The patient described the issue as a rash; the contributor is a female aged 18–29; present for less than one week; the lesion involves the leg; symptoms reported: darkening, enlargement, itching and bothersome appearance; Fitzpatrick skin type I; this is a close-up image.
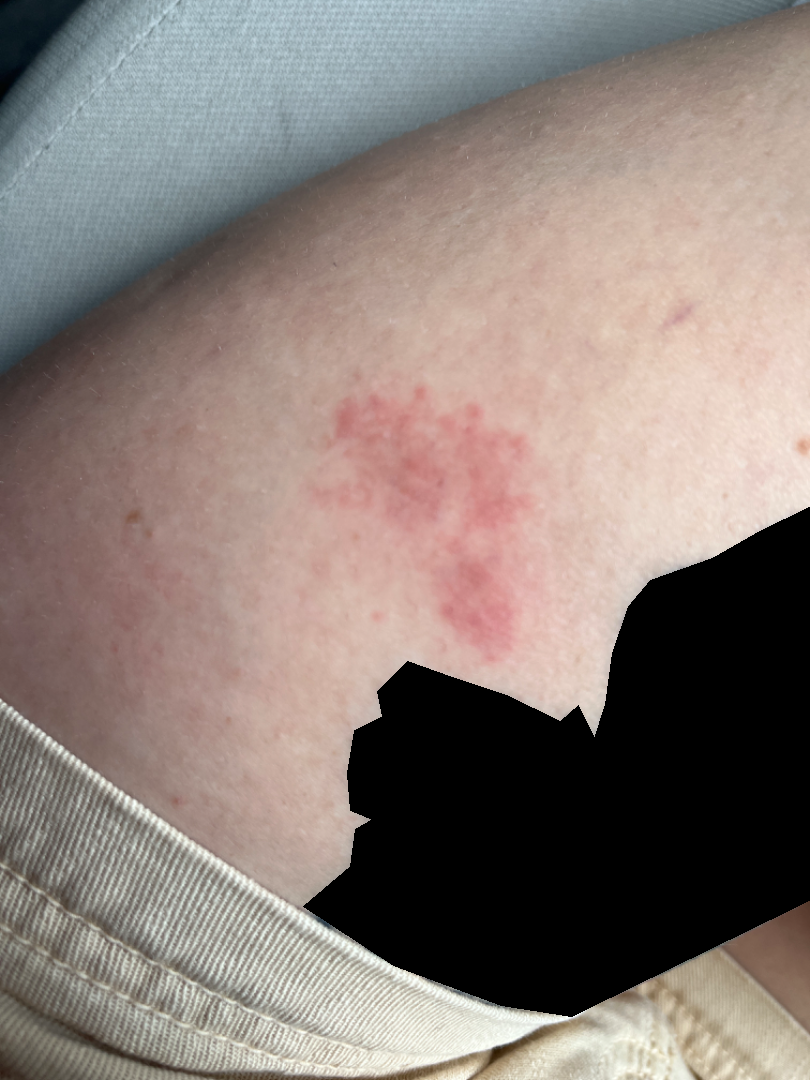A single dermatologist reviewed the case: the impression was split between Eczema and Allergic Contact Dermatitis.